A male subject, about 25 years old. A dermoscopic close-up of a skin lesion: 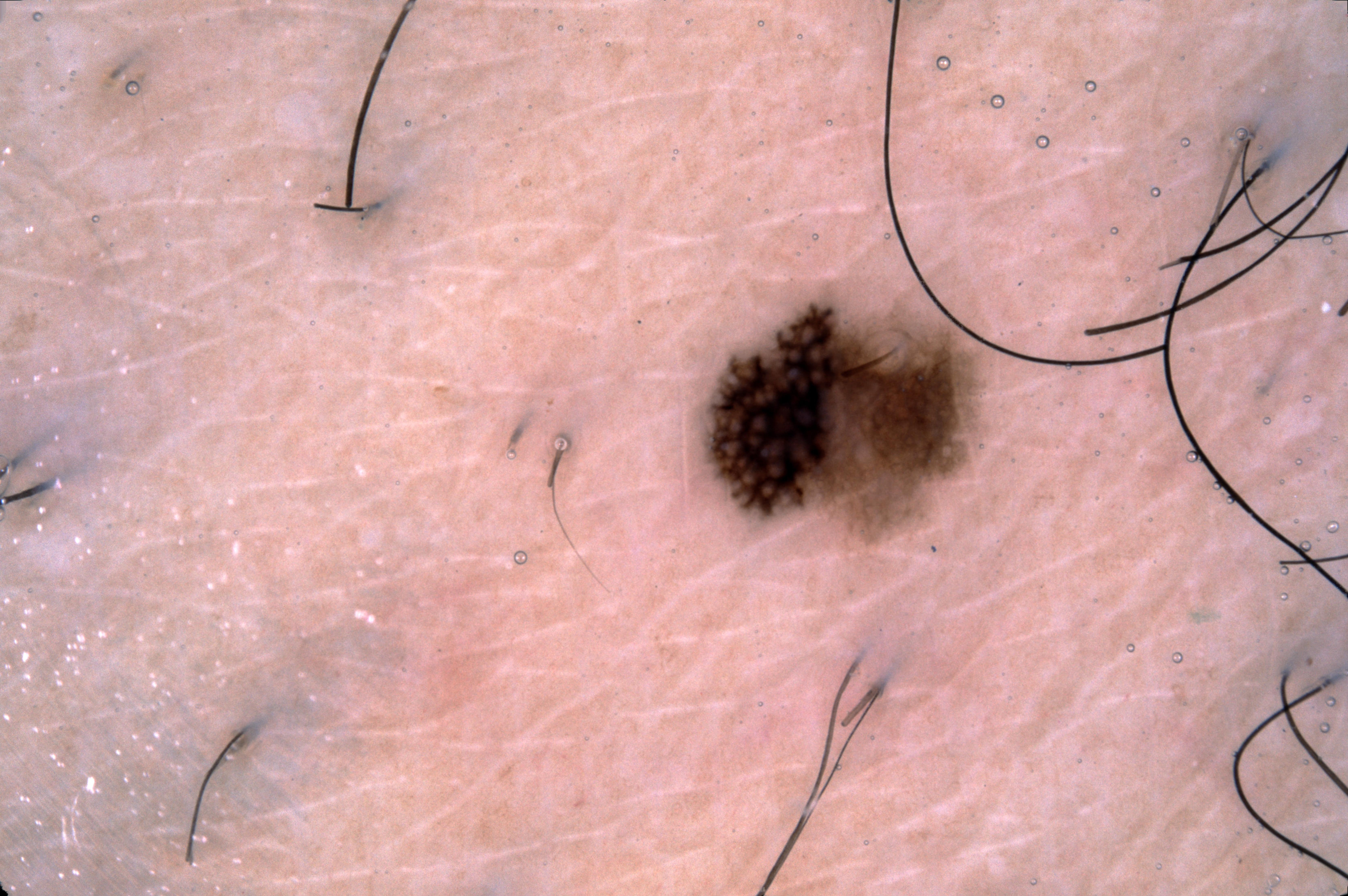A small lesion within a wider field of skin. Dermoscopy demonstrates pigment network. In (x1, y1, x2, y2) order, the lesion is bounded by 706, 308, 979, 532. Consistent with a melanocytic nevus.